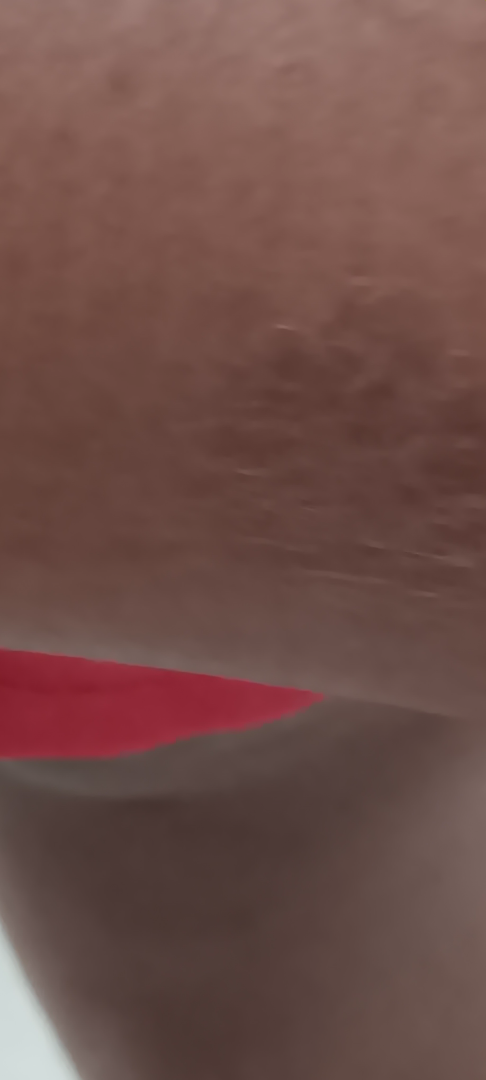Assessment: No differential diagnosis could be assigned on photographic review. Clinical context: The condition has been present for one to three months. The patient reported no relevant symptoms from the lesion. The patient notes the lesion is rough or flaky. Located on the leg. This is a close-up image. No associated systemic symptoms reported.